This is a close-up image: 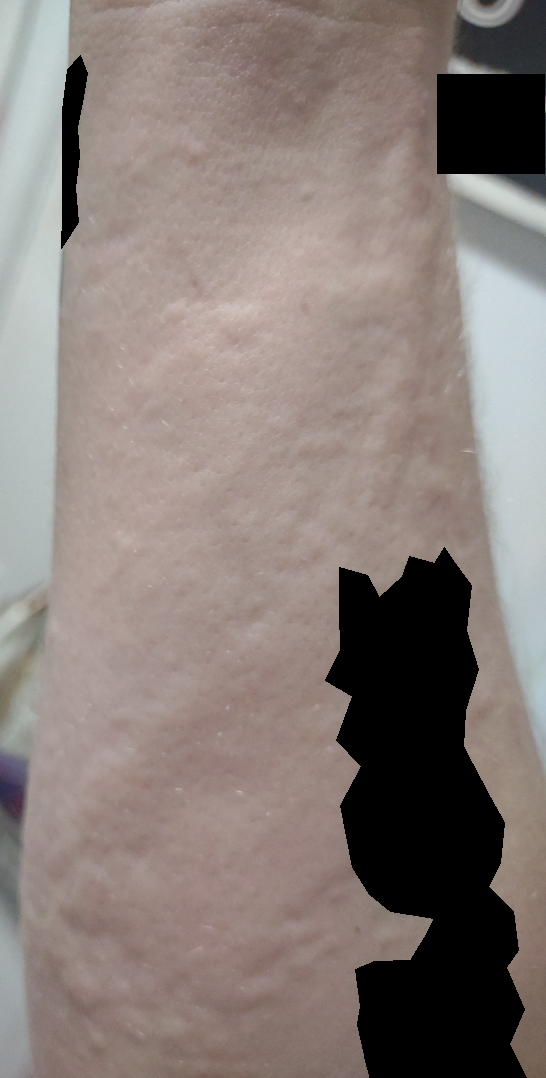Impression:
Single-reviewer assessment: most consistent with Urticaria.